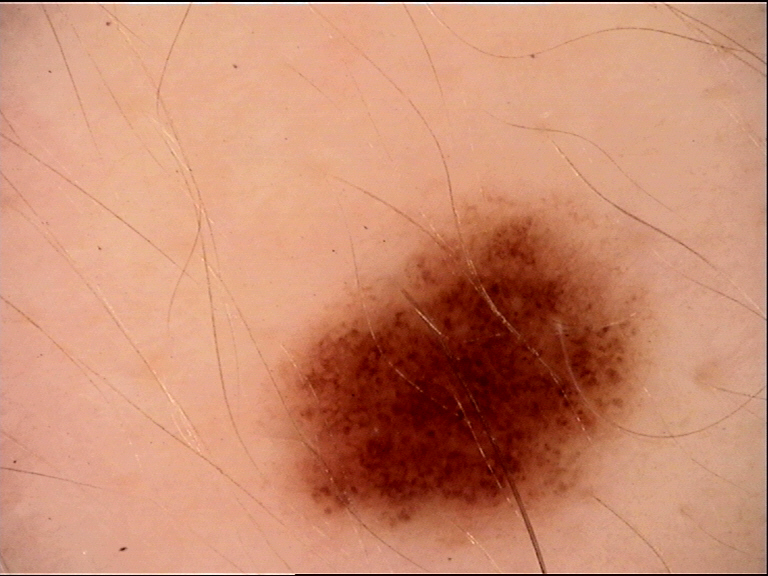diagnostic label: dysplastic compound nevus (expert consensus).